Skin tone: Fitzpatrick phototype V; human graders estimated a Monk skin tone scale of 5. A close-up photograph.
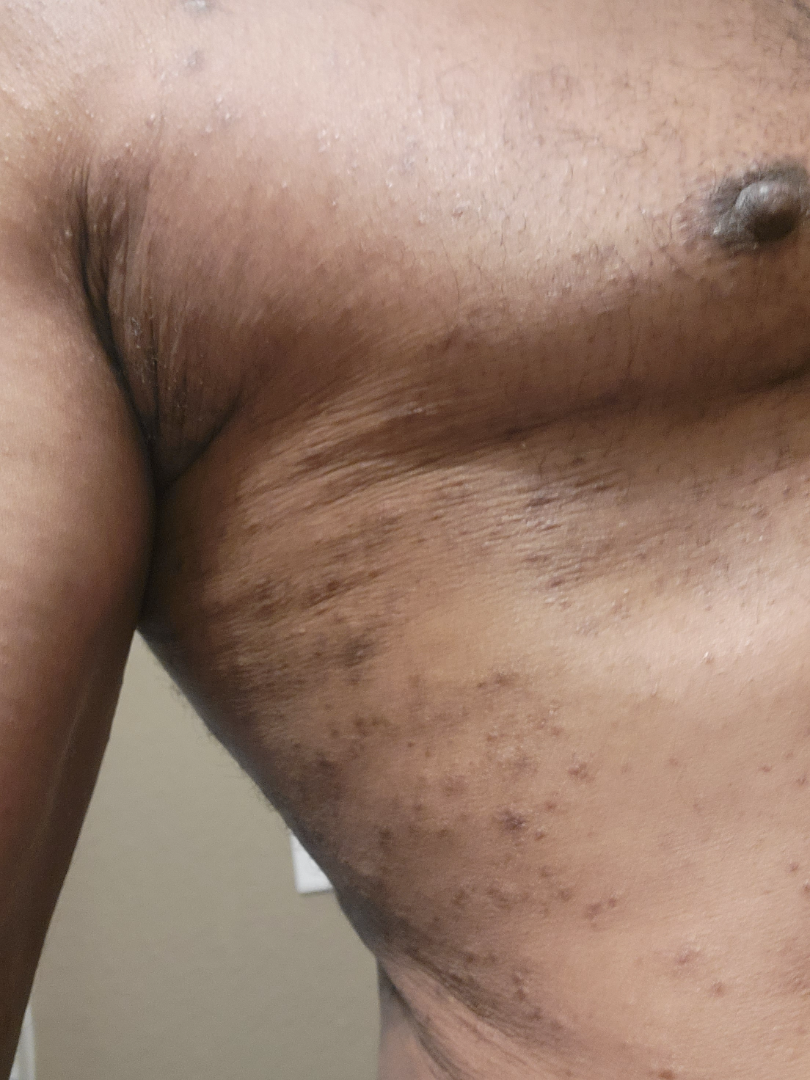Review: Diagnostic features were not clearly distinguishable in this photograph.